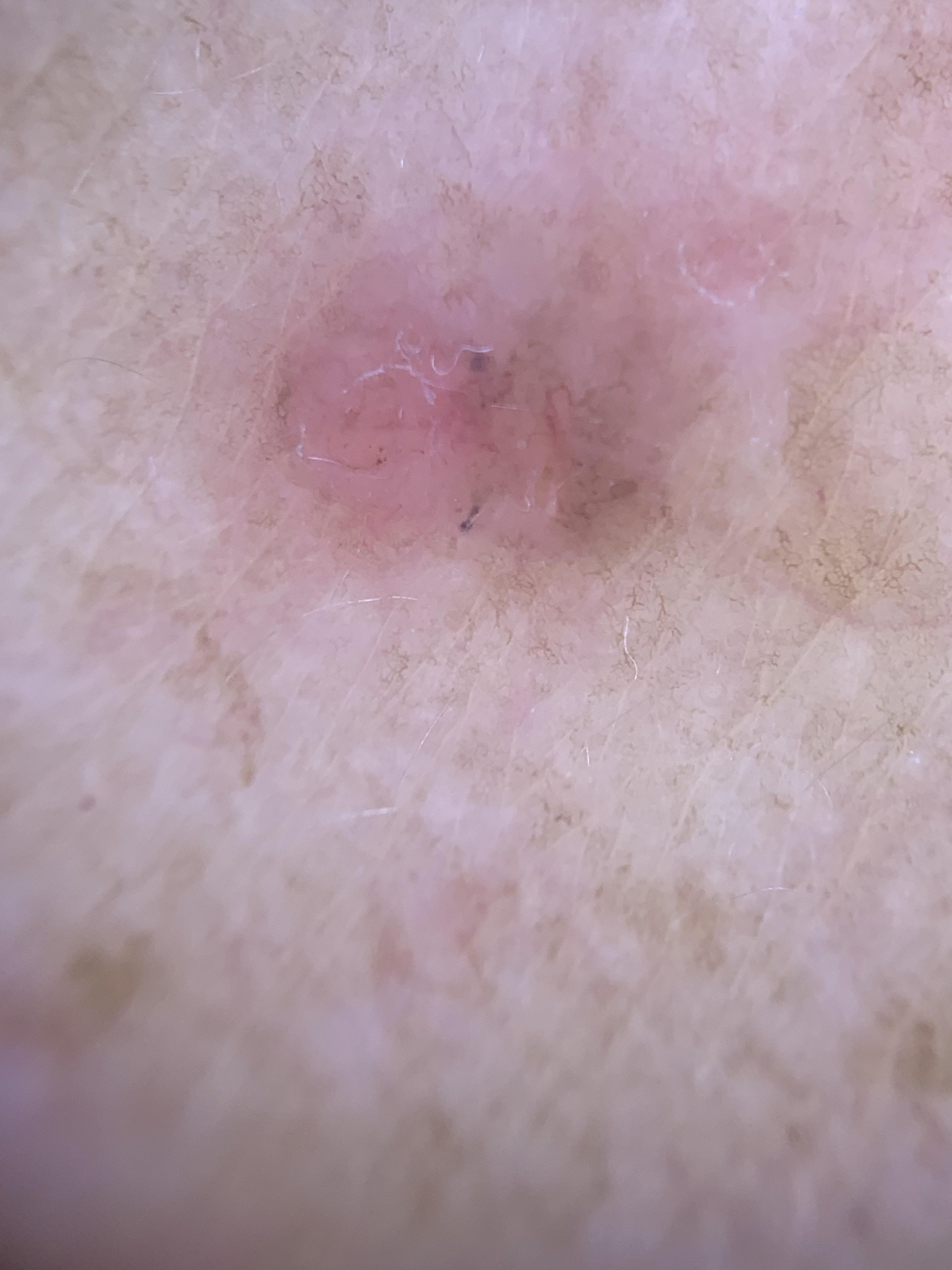The patient was assessed as FST II.
A male patient aged 83 or older.
Located on the trunk.
Histopathological examination showed a basal cell carcinoma.